The affected area is the arm. The patient is 18–29, female. The photo was captured at an angle — 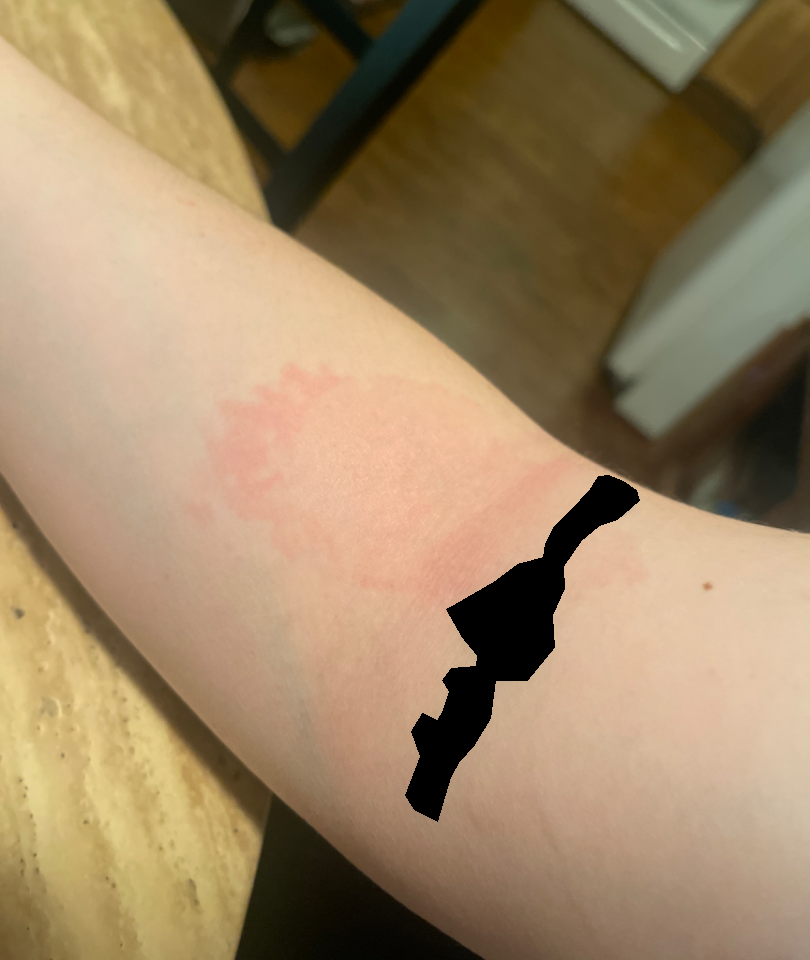Impression: On remote review of the image, most likely Eczema; also raised was Allergic Contact Dermatitis.